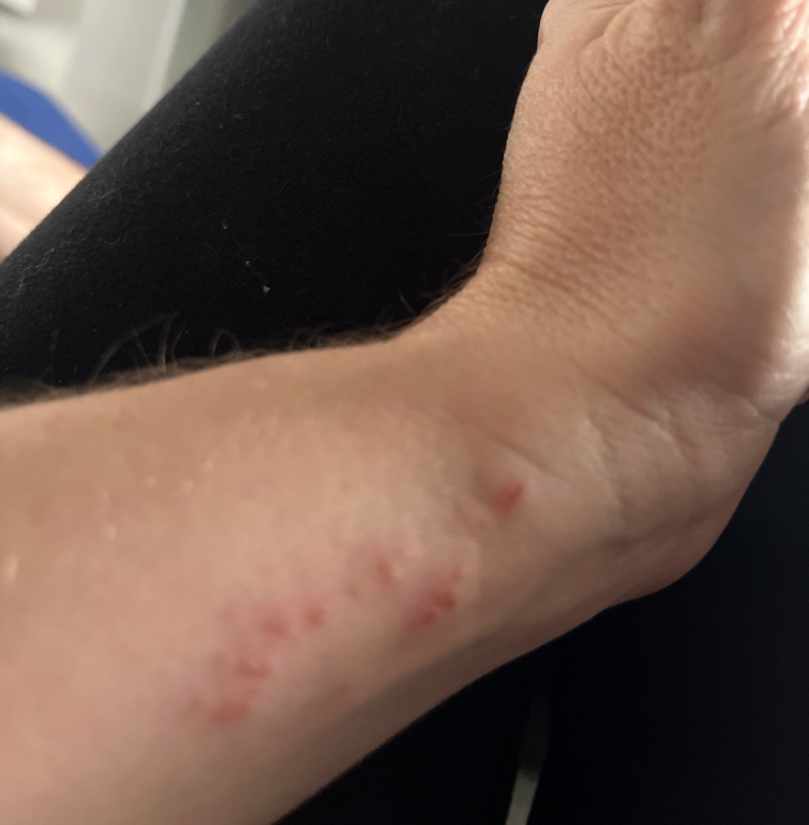Q: What was the assessment?
A: ungradable on photographic review
Q: Age and sex?
A: female, age 40–49
Q: How was the photo taken?
A: at an angle
Q: Anatomic location?
A: front of the torso, head or neck, back of the torso and arm